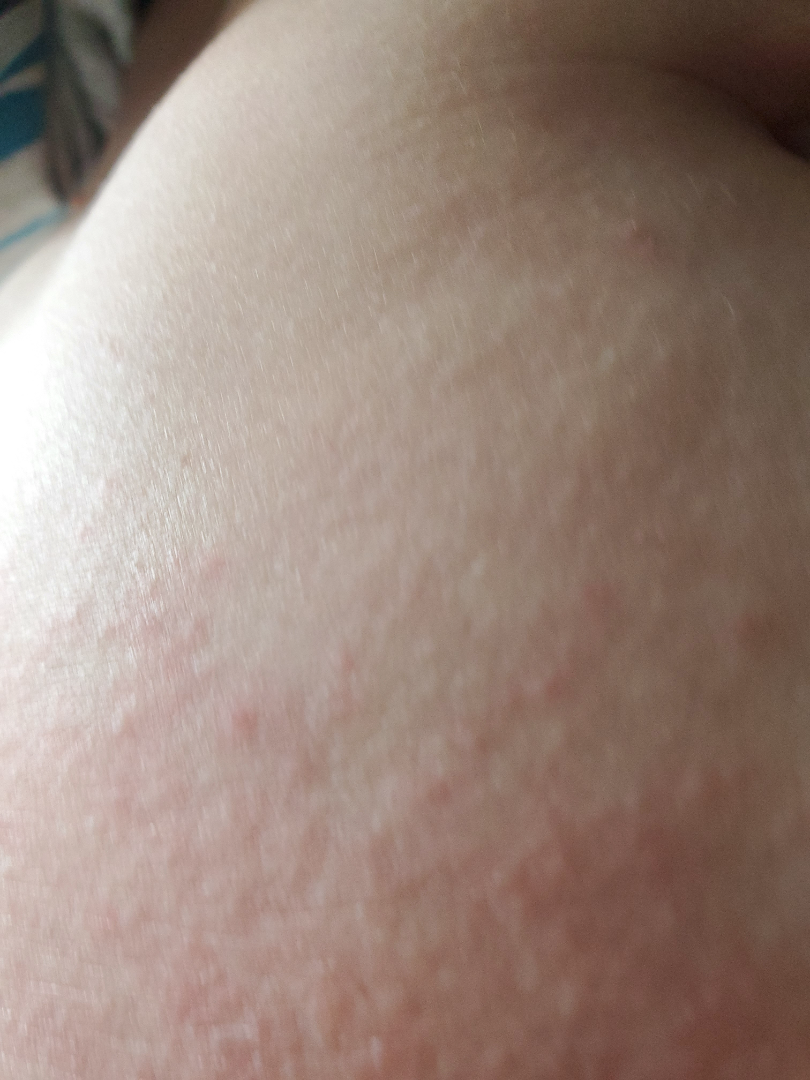The photograph is a close-up of the affected area.
On photographic review, the reviewer's impression was Eczema.